A skin lesion imaged with a dermatoscope.
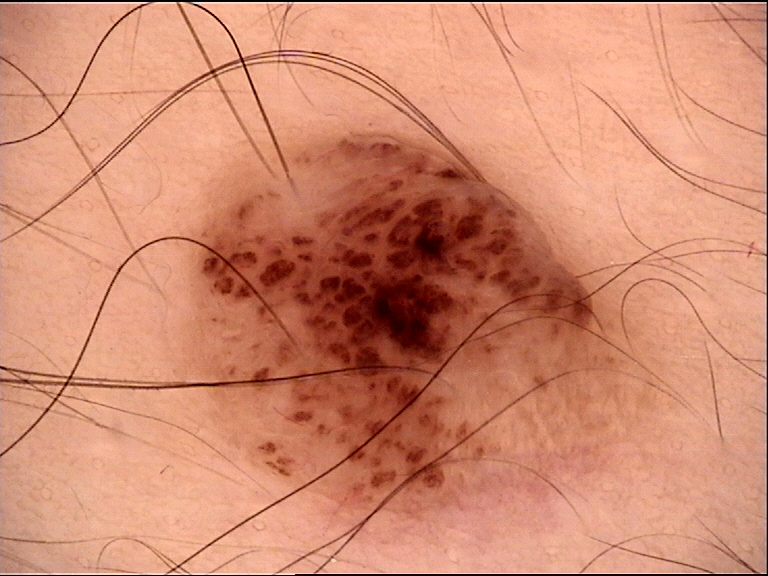The morphology is that of a banal lesion.
Diagnosed as a dermal nevus.